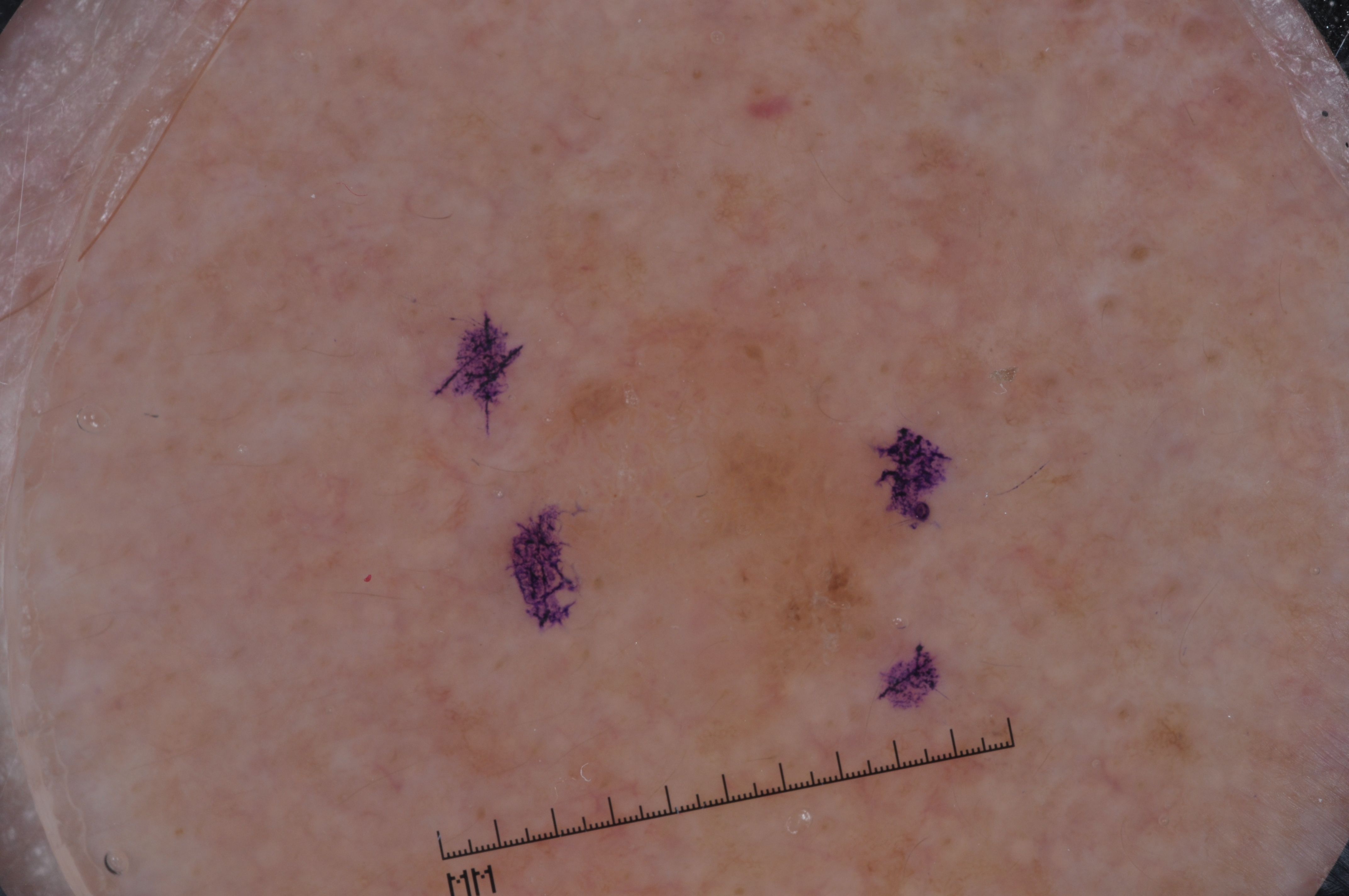Image and clinical context: Dermoscopy of a skin lesion. A male patient, aged 63 to 67. As (left, top, right, bottom), the lesion's extent is box(421, 307, 948, 794). Dermoscopic examination shows no negative network, pigment network, streaks, or milia-like cysts. Impression: Diagnosed as a seborrheic keratosis, a benign lesion.